A dermoscopic photograph of a skin lesion. The patient is Fitzpatrick phototype I. A male patient approximately 85 years of age or older — 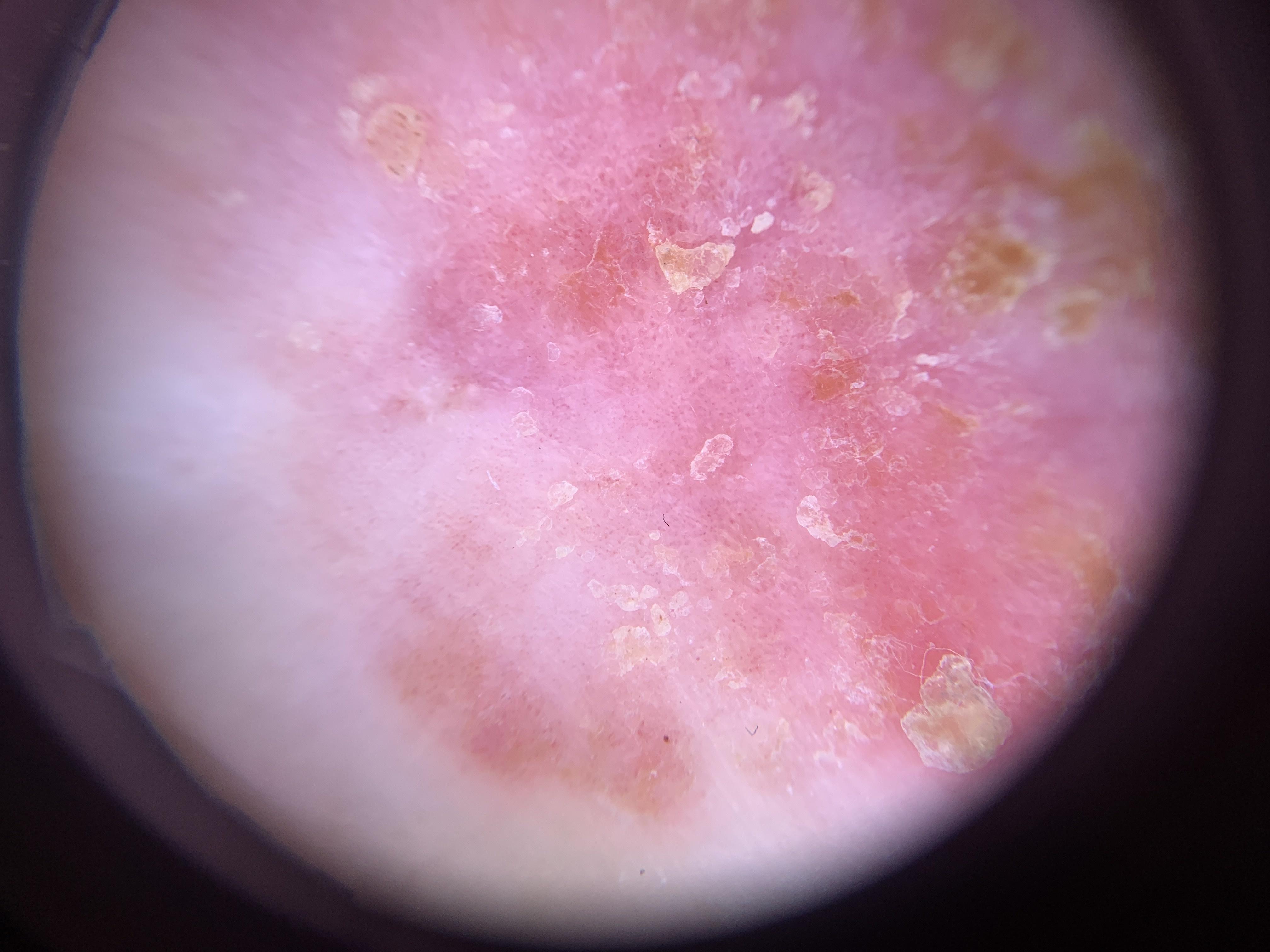Diagnosis: Histopathologically confirmed as a malignant, epidermal lesion — a squamous cell carcinoma.